Symptoms reported: itching · the patient is a female aged 18–29 · the affected area is the arm · close-up view · the patient considered this a rash · texture is reported as raised or bumpy · present for about one day — 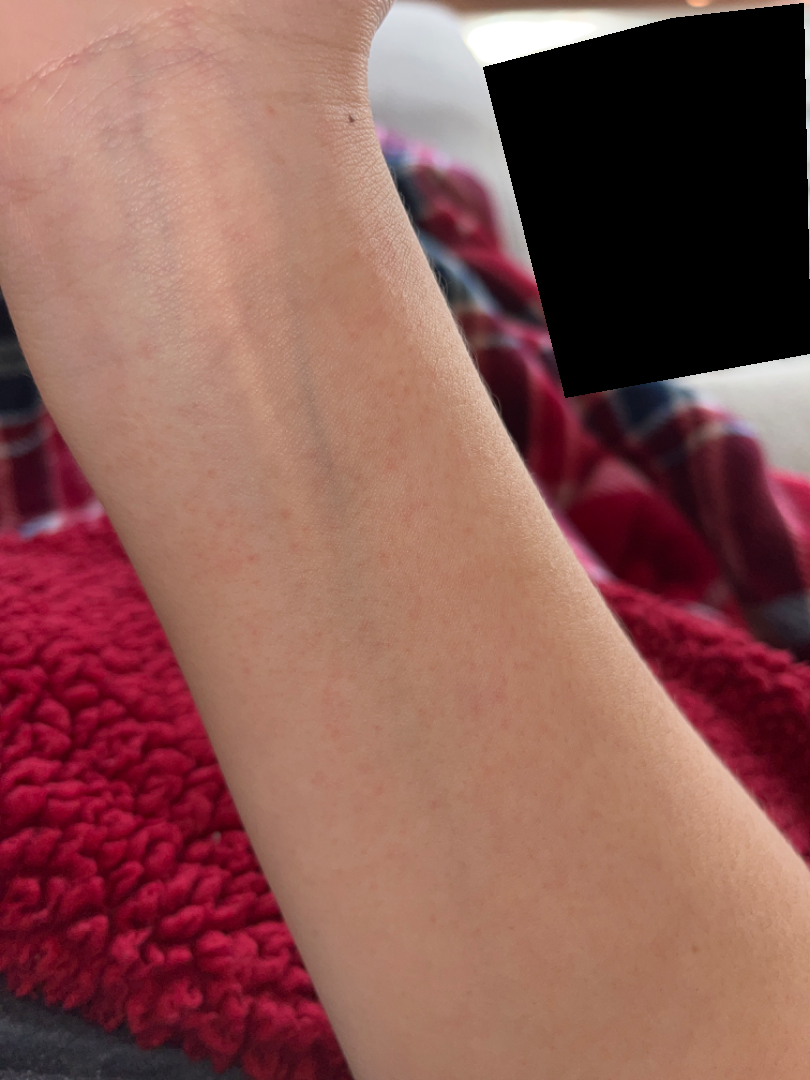Most likely Irritant Contact Dermatitis; an alternative is Acute dermatitis, NOS.